The lesion is associated with enlargement and bothersome appearance. The front of the torso is involved. The photo was captured at an angle. Texture is reported as raised or bumpy. The patient considered this a rash: 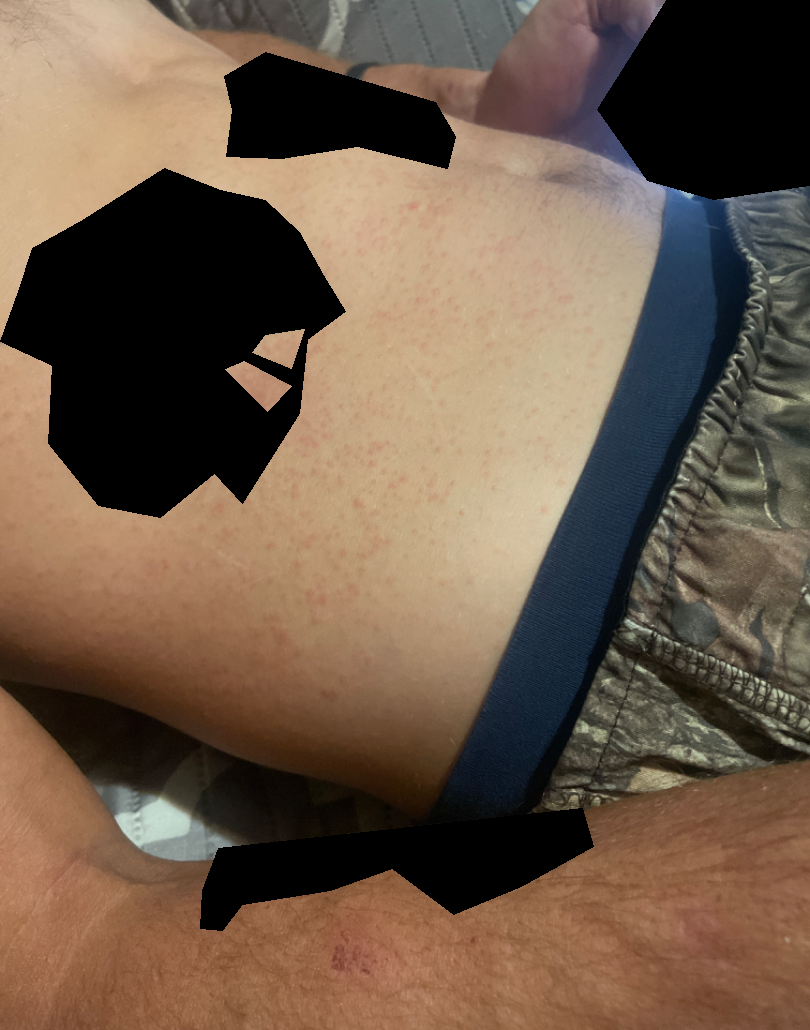{"differential": {"tied_lead": ["Drug Rash", "Viral Exanthem"], "unlikely": ["Miliaria"]}}